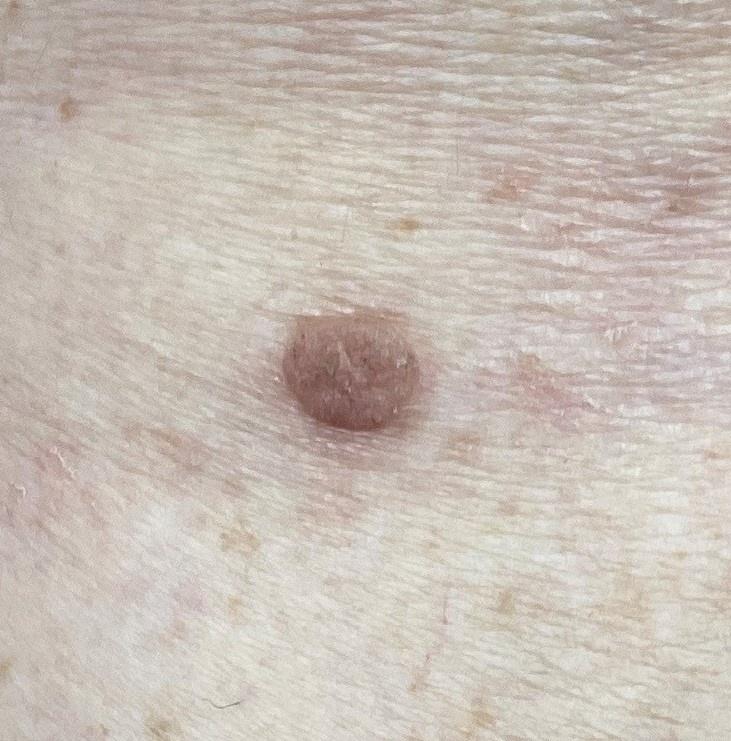Summary: The patient is FST II. A female patient aged 78 to 82. A clinical photograph of a skin lesion. Located on a lower extremity. Diagnosis: Histopathologically confirmed as a benign, epidermal lesion — a seborrheic keratosis.